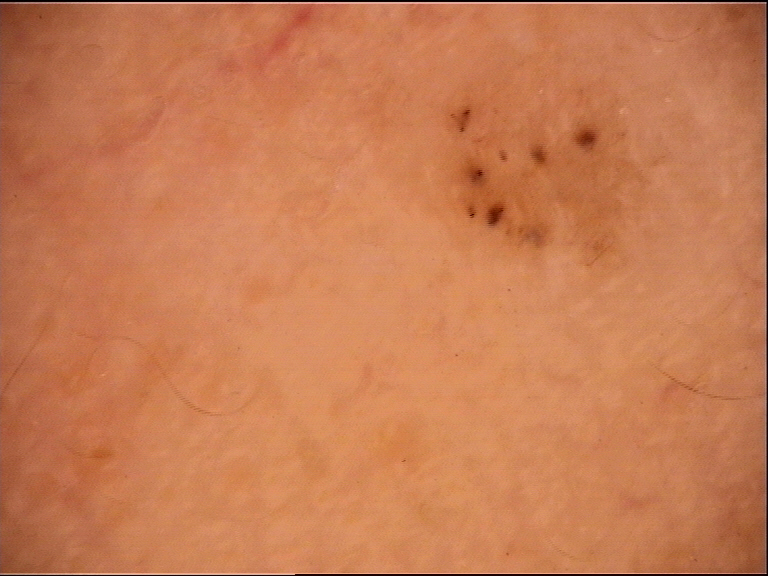Histopathology confirmed a basal cell carcinoma.